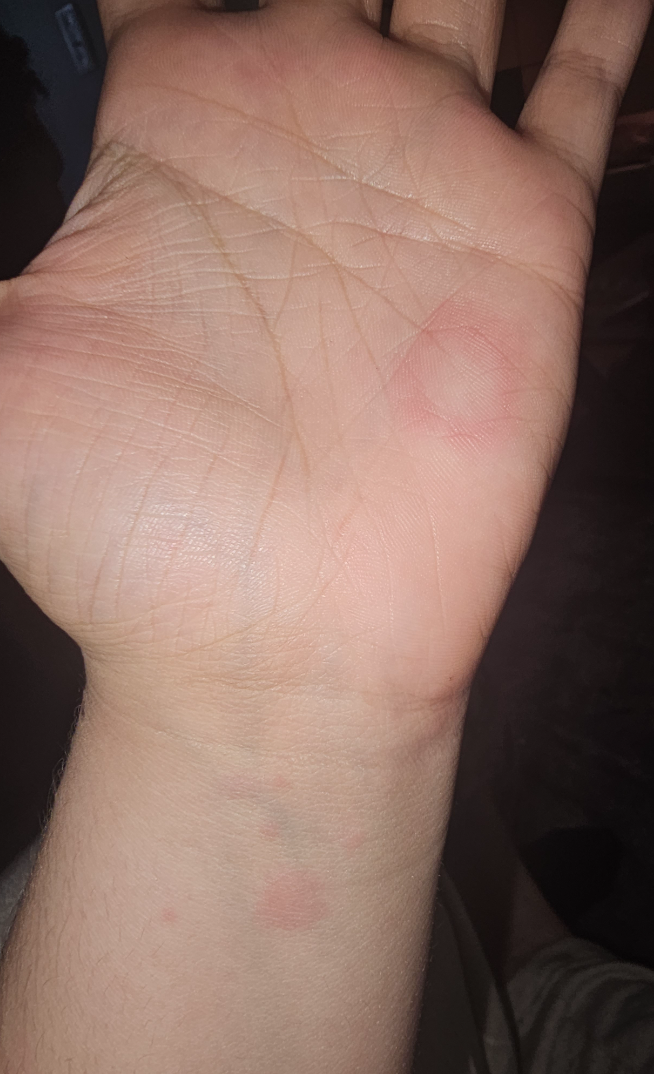The photograph is a close-up of the affected area.
The lesion is described as raised or bumpy.
The lesion involves the top or side of the foot, palm, back of the hand, arm and sole of the foot.
Reported duration is more than one year.
Self-categorized by the patient as a rash.
The patient notes pain, itching and burning.
The contributor is 18–29, female.
Skin tone: Fitzpatrick skin type II; human graders estimated a MST of 2.
The reviewing dermatologist's impression was: the differential includes Drug Rash, Urticaria and Erythema multiforme, with no clear leading consideration.